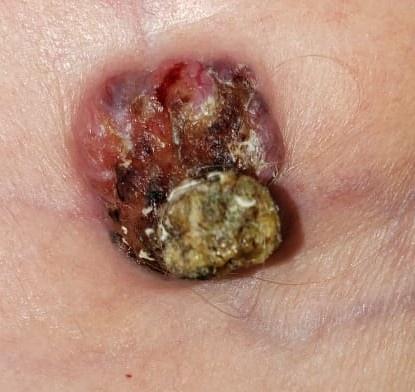Q: What are the patient's age and sex?
A: female, roughly 85 years of age or older
Q: What kind of image is this?
A: clinical overview photograph
Q: What Fitzpatrick skin type was recorded?
A: II
Q: What is the diagnosis?
A: Squamous cell carcinoma (biopsy-proven)